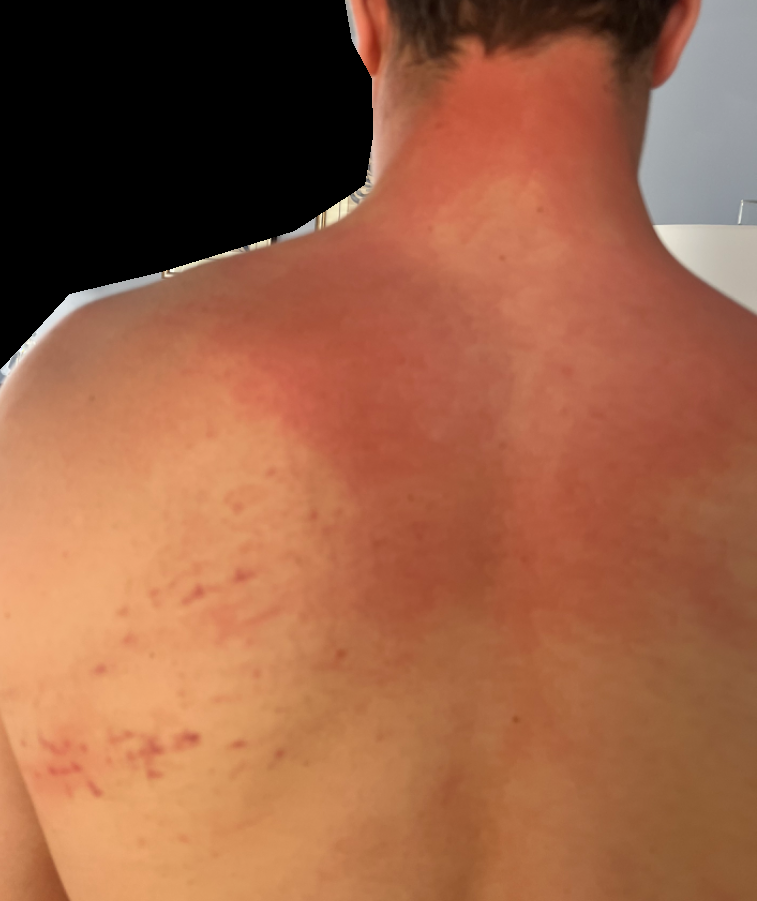Case summary:
• assessment · unable to determine
• shot type · at an angle
• symptoms · darkening
• self-categorized as · skin that appeared healthy to them
• skin tone · Fitzpatrick phototype II
• described texture · flat
• site · back of the torso
• associated systemic symptoms · none reported